A dermoscopic image of a skin lesion.
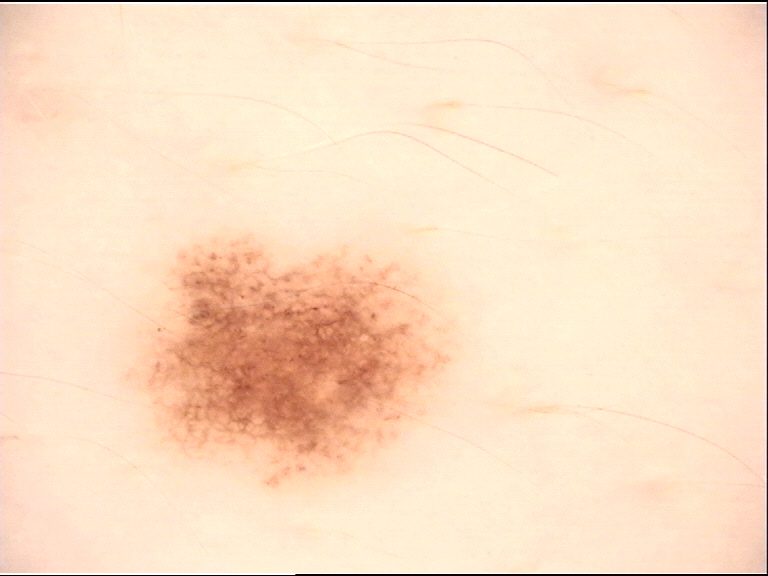diagnosis — dysplastic junctional nevus (expert consensus).